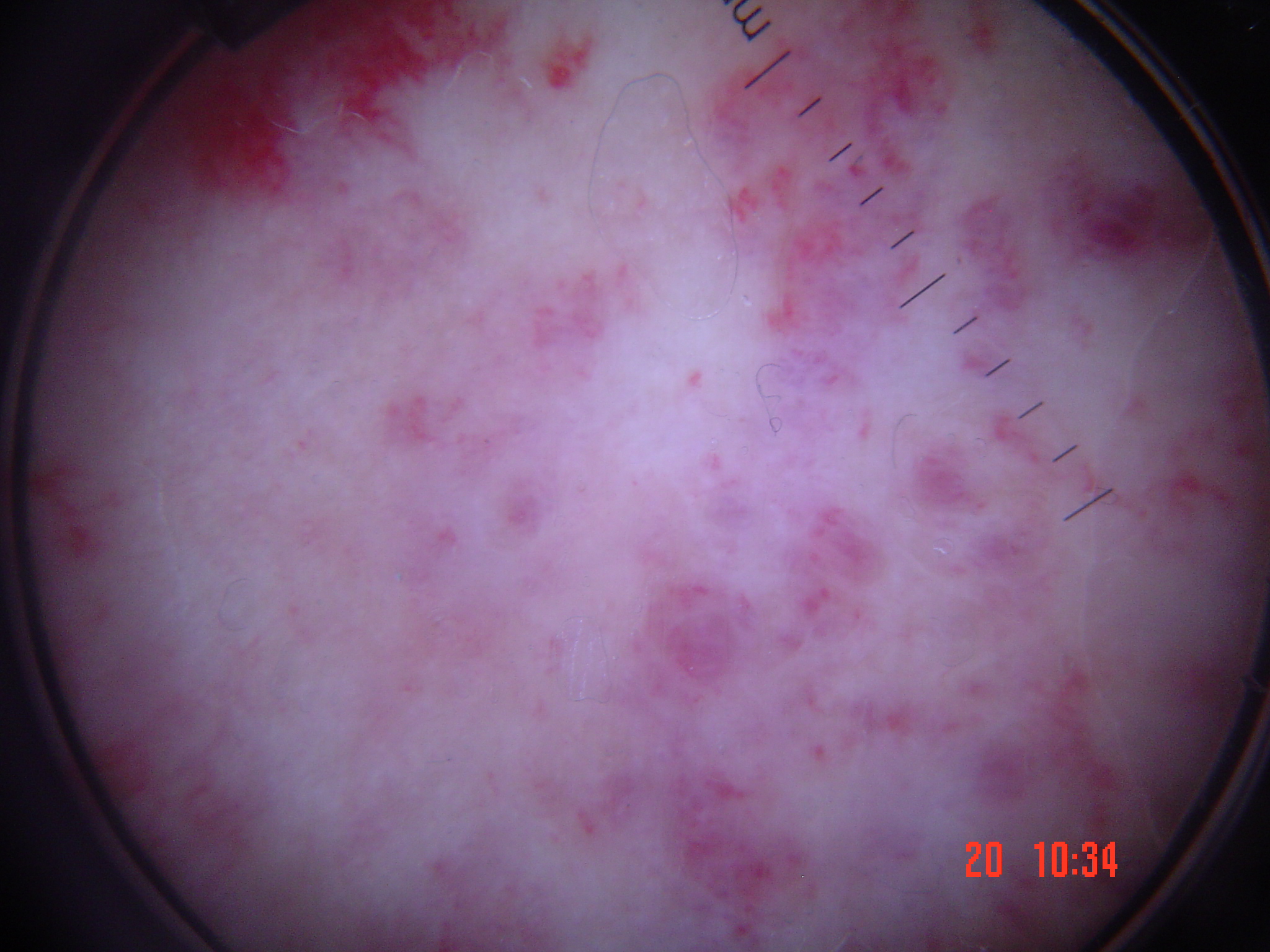Diagnosed as a hemangioma.